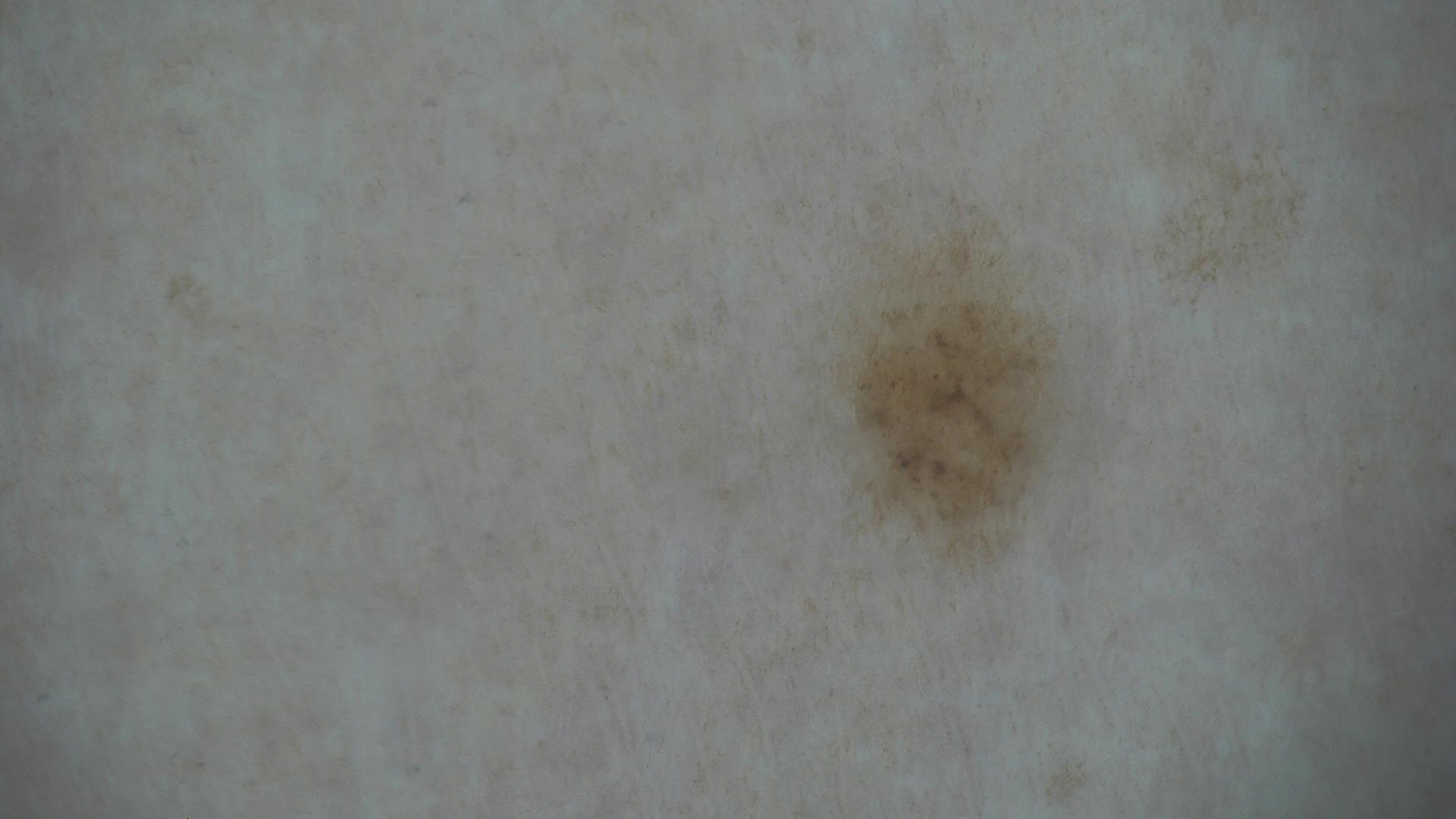| key | value |
|---|---|
| image type | dermoscopy |
| label | dysplastic junctional nevus (expert consensus) |